A dermoscopic image of a skin lesion; a female patient, aged 43 to 47.
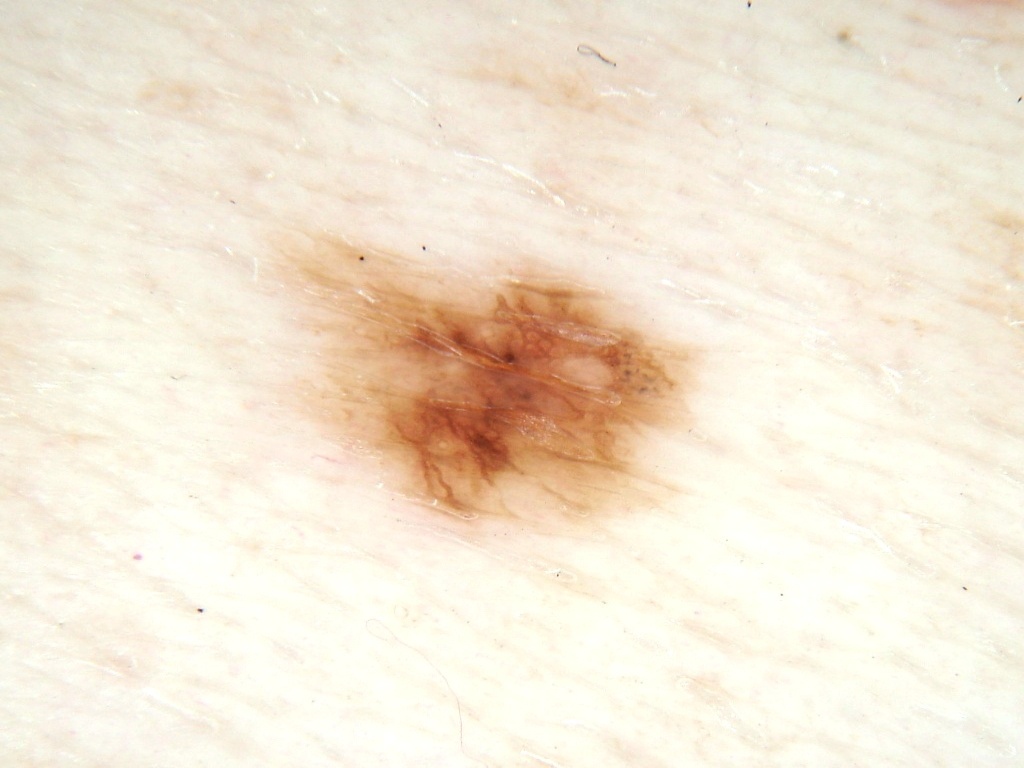Notes:
– lesion bbox — [268,223,700,538]
– lesion extent — moderate
– features — pigment network; absent: negative network, milia-like cysts, streaks, and globules
– diagnosis — a melanocytic nevus